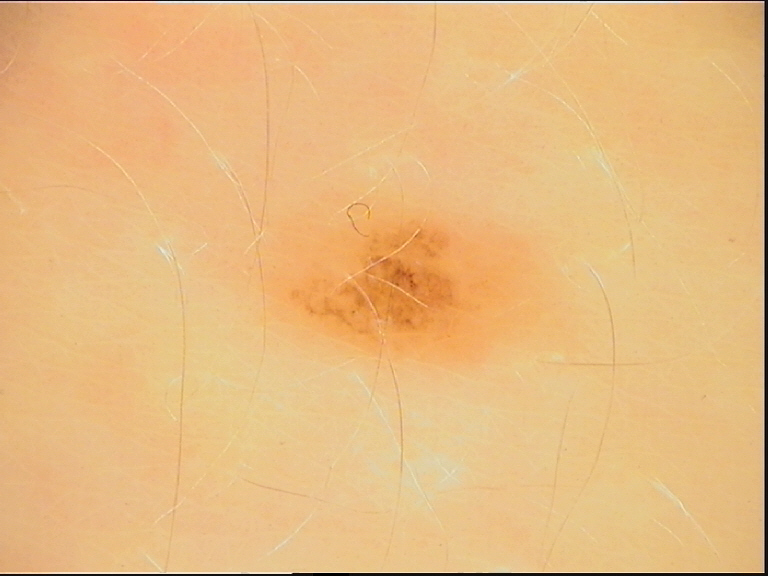A skin lesion imaged with a dermatoscope.
Labeled as a dysplastic junctional nevus.